A dermoscopic photograph of a skin lesion.
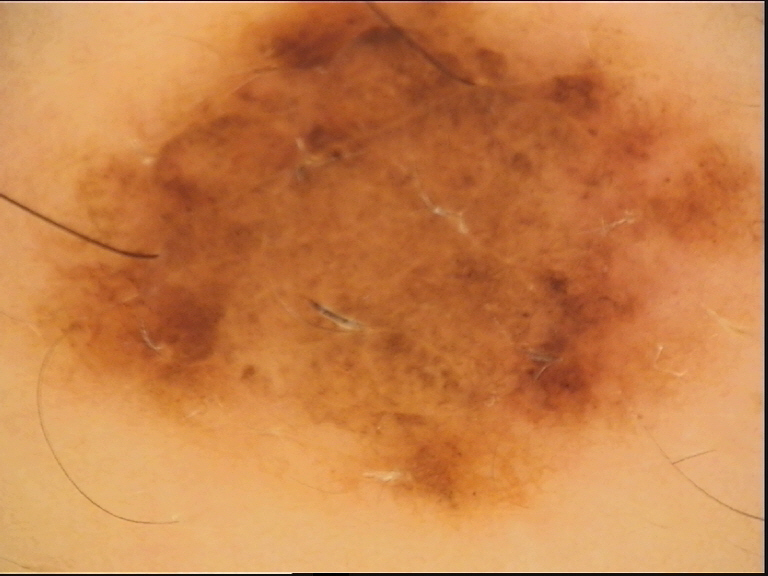Conclusion: The diagnostic label was a benign lesion — a dysplastic compound nevus.